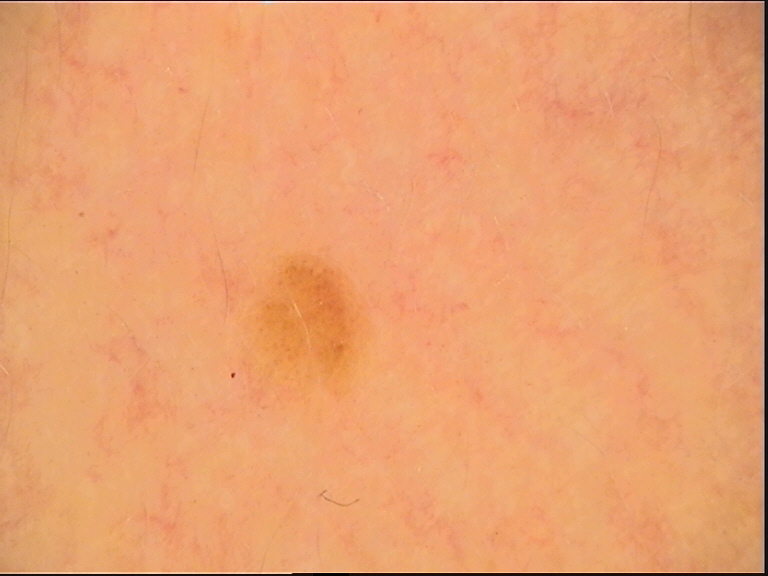Conclusion:
The diagnosis was a dysplastic junctional nevus.